The photograph is a close-up of the affected area · female subject, age 50–59 · the leg is involved:
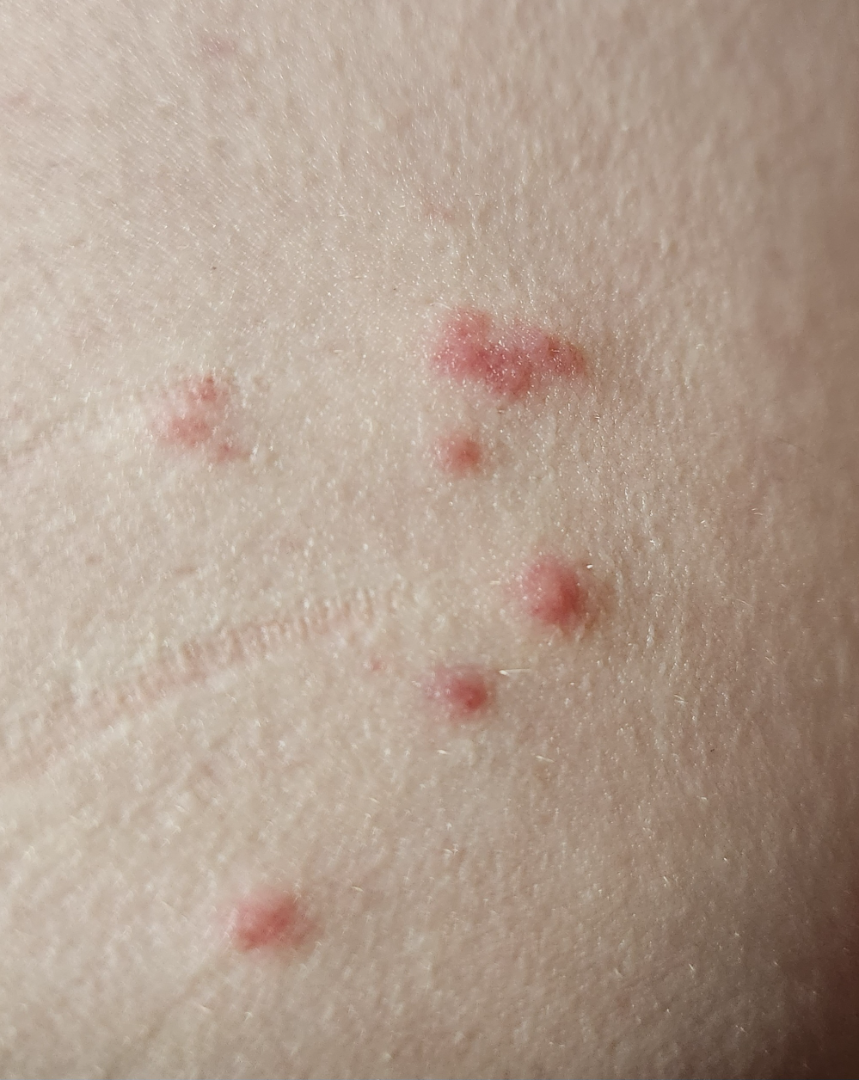Assessment:
No differential diagnosis could be assigned on photographic review.